The patient reports the condition has been present for about one day · no associated systemic symptoms reported · the lesion involves the back of the torso and front of the torso · the patient reports the lesion is raised or bumpy · the photo was captured at an angle · reported lesion symptoms include burning, enlargement, itching and pain: 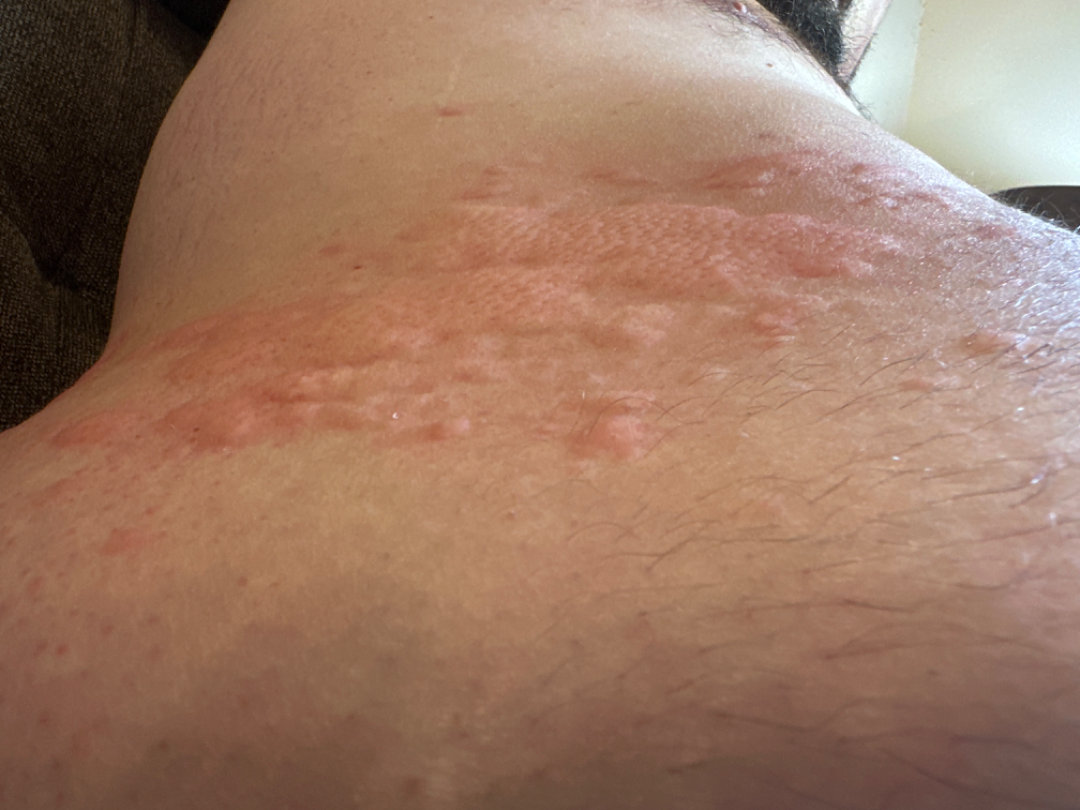In keeping with Urticaria.